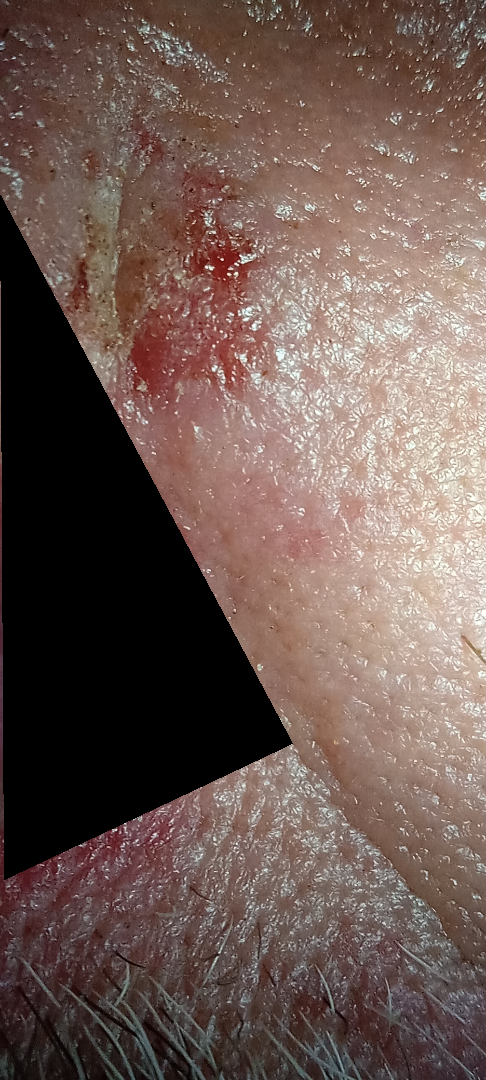Q: Could the case be diagnosed?
A: none discernible
Q: Constitutional symptoms?
A: joint pain
Q: What is the framing?
A: close-up
Q: Who is the patient?
A: male, age 50–59
Q: Reported symptoms?
A: enlargement
Q: What is the lesion texture?
A: raised or bumpy and rough or flaky
Q: Where on the body?
A: head or neck
Q: How does the patient describe it?
A: a growth or mole